The photograph was taken at a distance; the affected area is the leg; female contributor, age 50–59 — 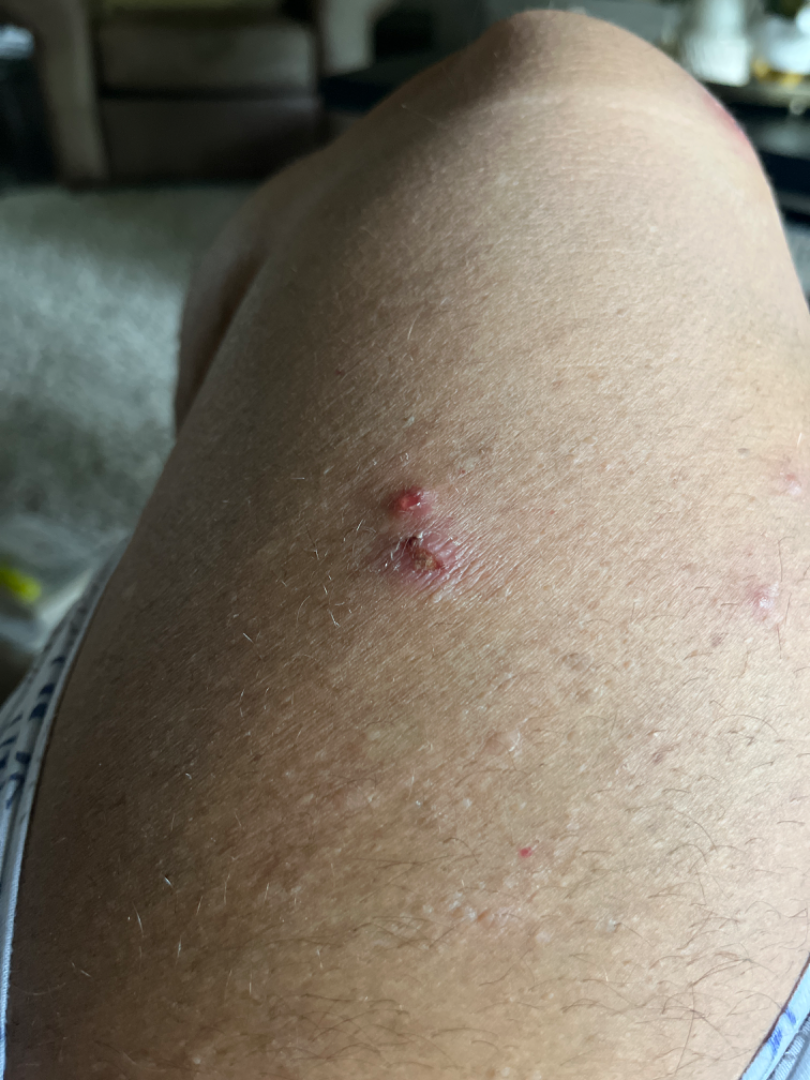- assessment — not assessable
- systemic symptoms — joint pain
- present for — one to four weeks
- symptoms — enlargement, bleeding, bothersome appearance, pain and itching
- described texture — fluid-filled and raised or bumpy
- self-categorized as — a rash